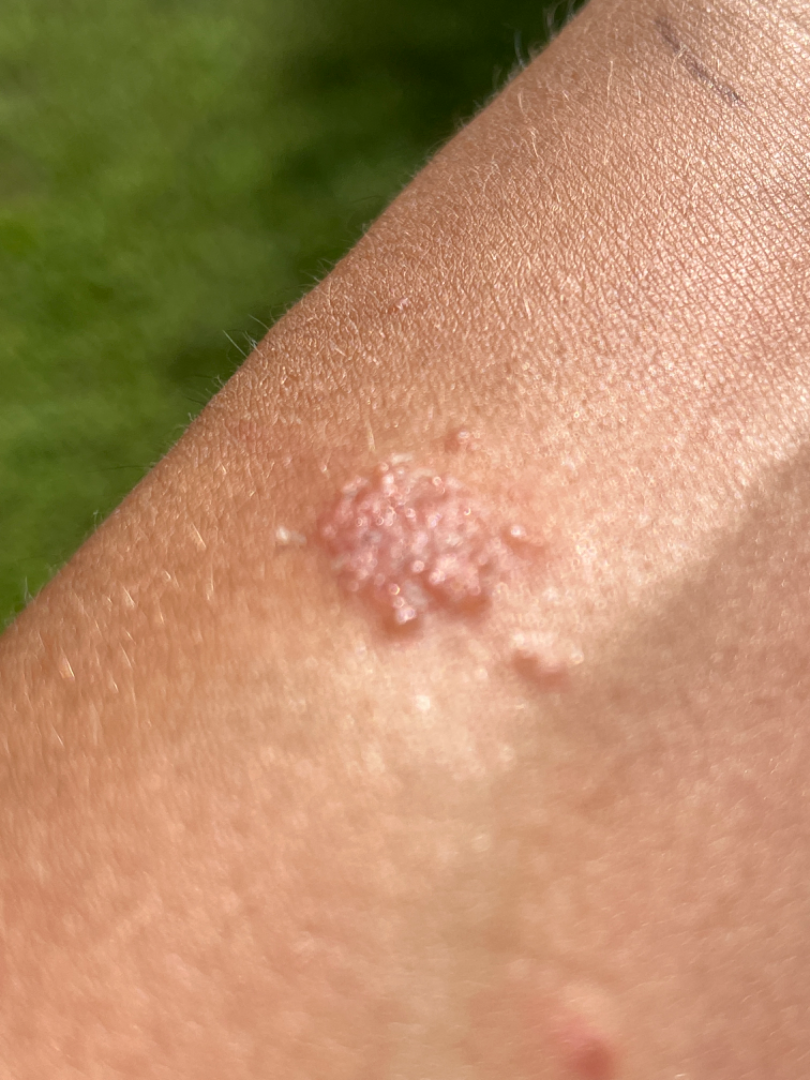– assessment · unable to determine
– photo taken · close-up